The contributor is 30–39, female · the lesion involves the head or neck, front of the torso and leg · a close-up photograph — 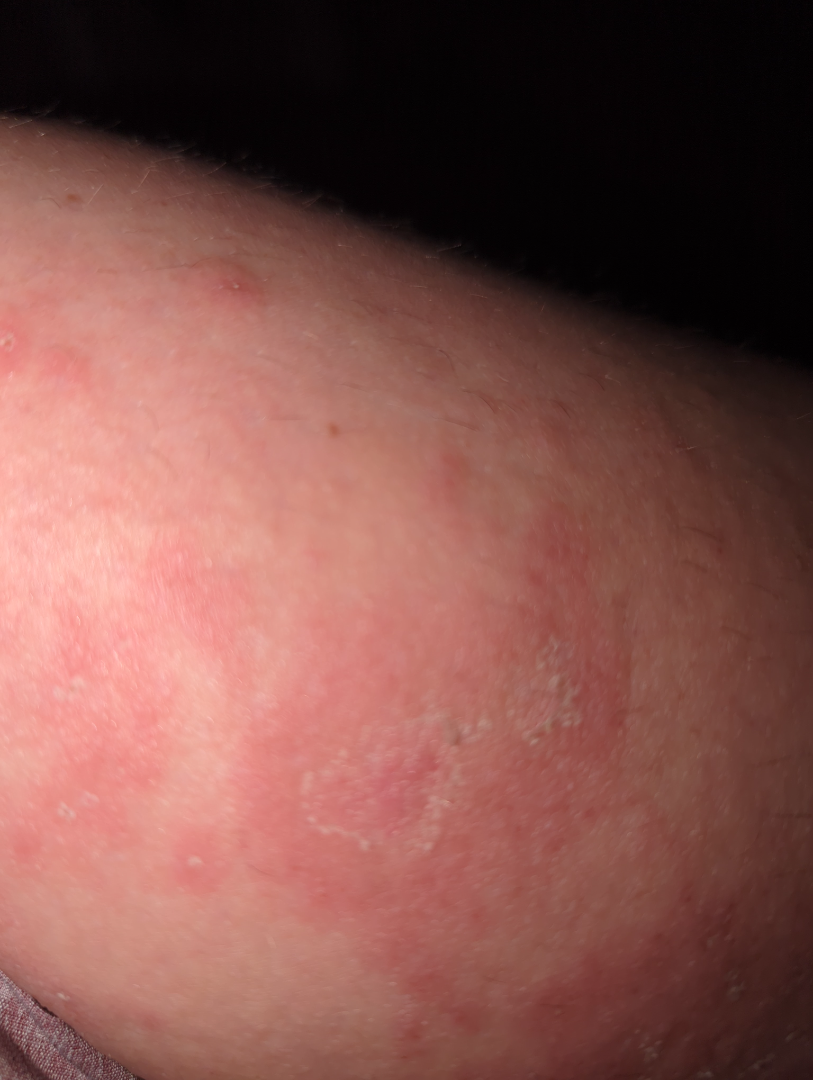assessment: not assessable
texture: rough or flaky
symptoms:
  - itching
  - enlargement
duration: one to four weeks
patient_category: a rash